Close-up view; the back of the torso, leg, front of the torso, arm and head or neck are involved: 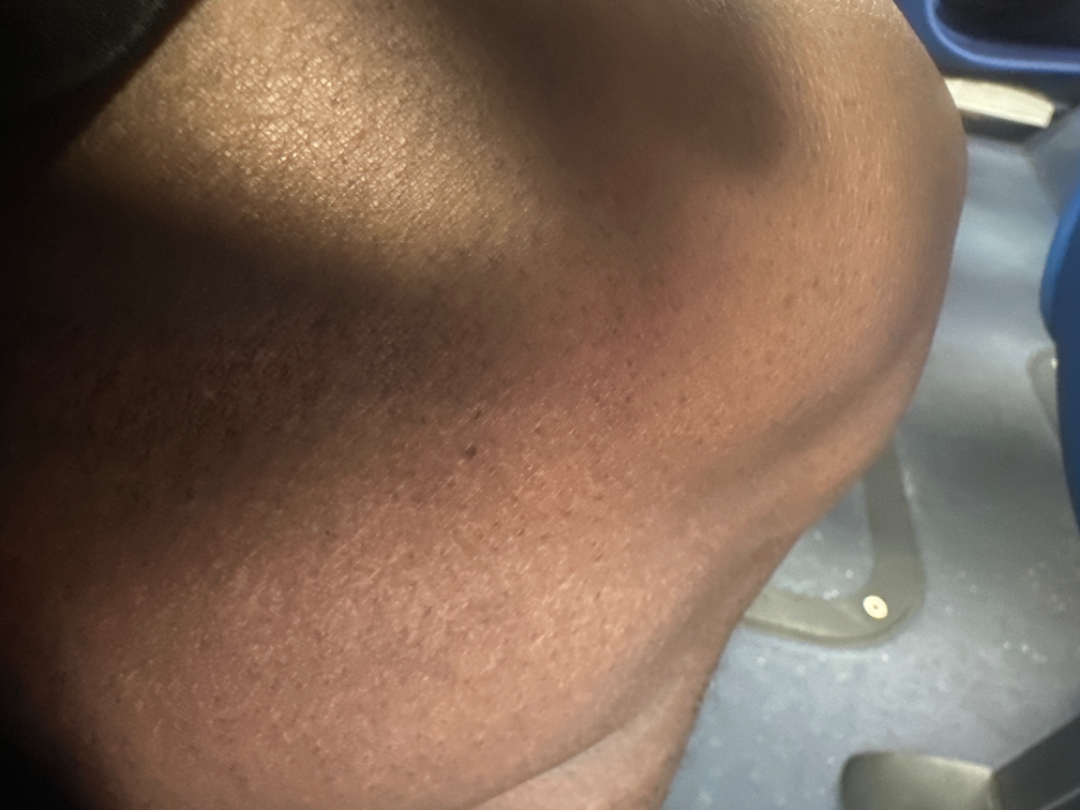<report>
  <assessment>unable to determine</assessment>
</report>